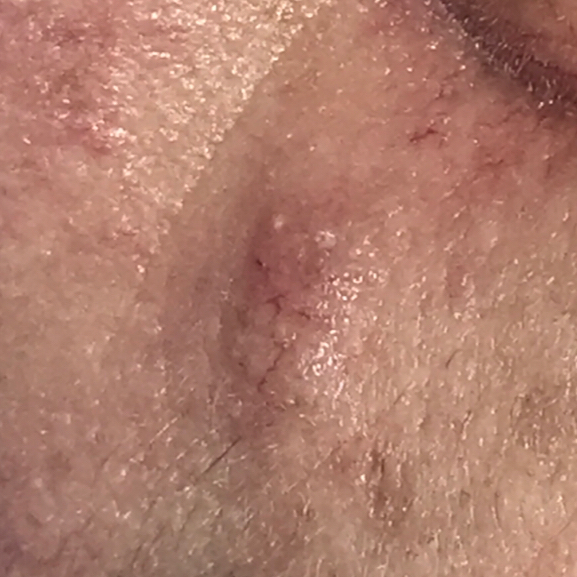A clinical photograph of a skin lesion. A female patient in their 30s. Fitzpatrick skin type II. History notes pesticide exposure and prior skin cancer (patient or family). The lesion was found on the face. Measuring about 8 × 5 mm. The patient describes that the lesion is elevated. Histopathologically confirmed as a skin cancer — a basal cell carcinoma.